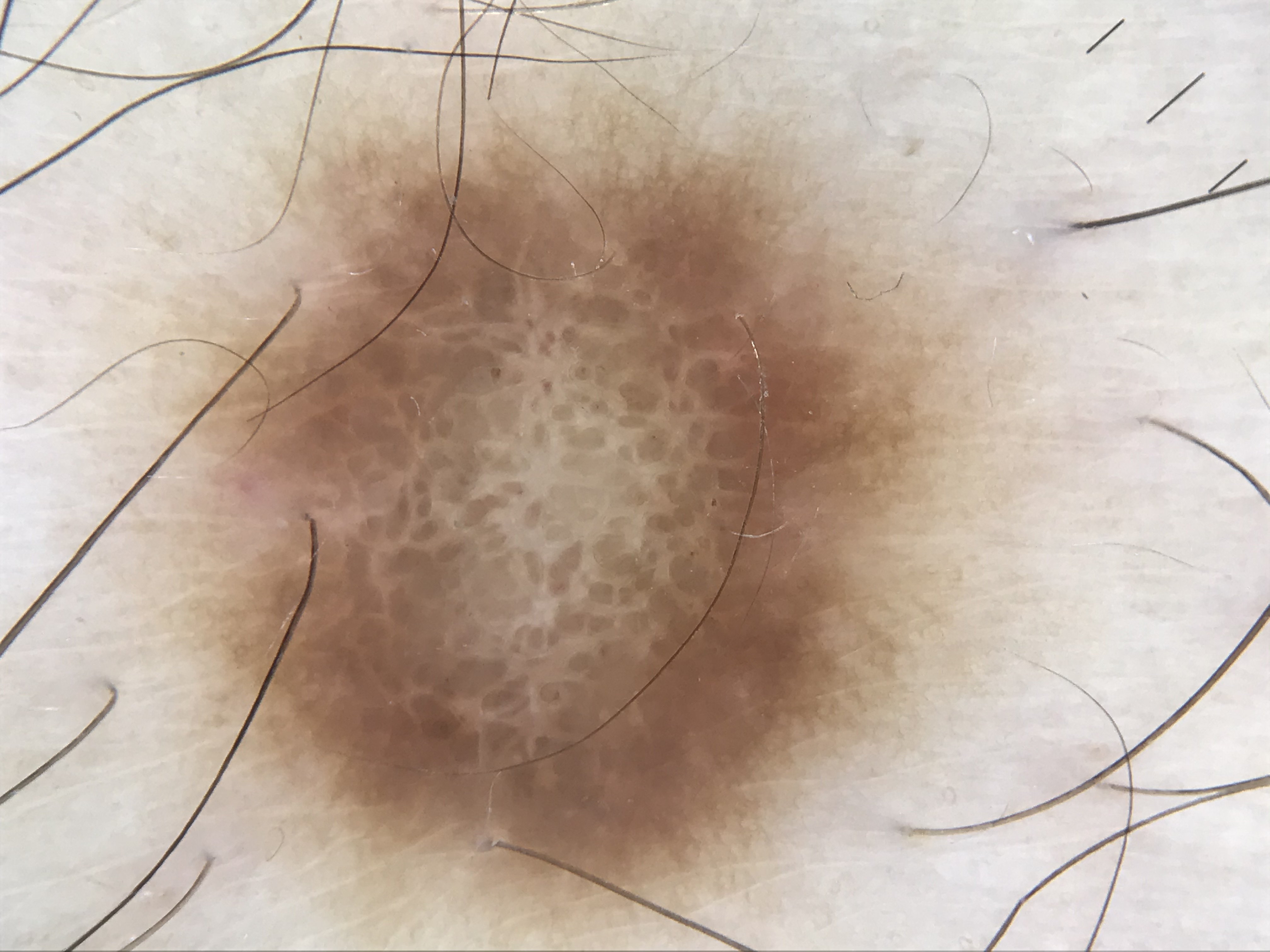| key | value |
|---|---|
| assessment | dermatofibroma (expert consensus) |